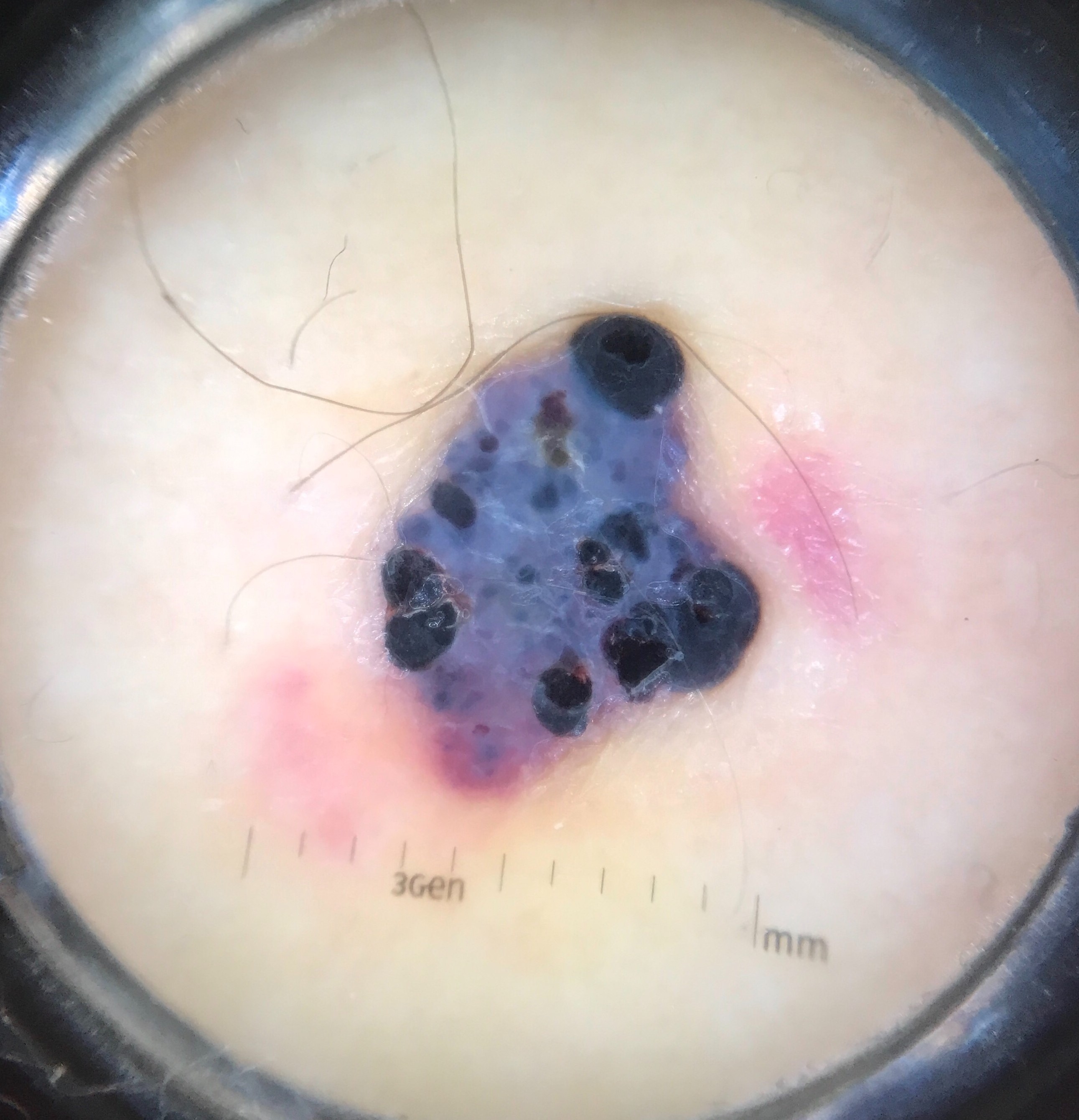imaging — dermoscopy | category — vascular | label — angiokeratoma (expert consensus).